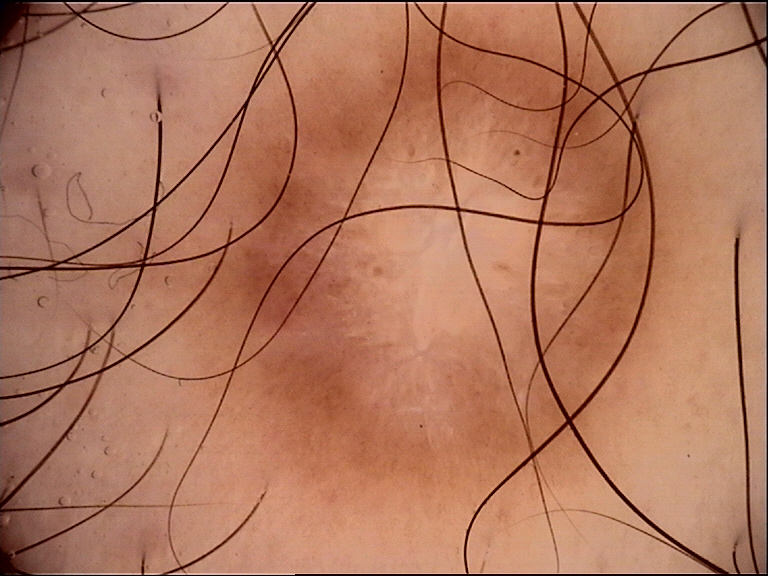class — dermatofibroma (expert consensus).